A clinical photo of a skin lesion taken with a smartphone.
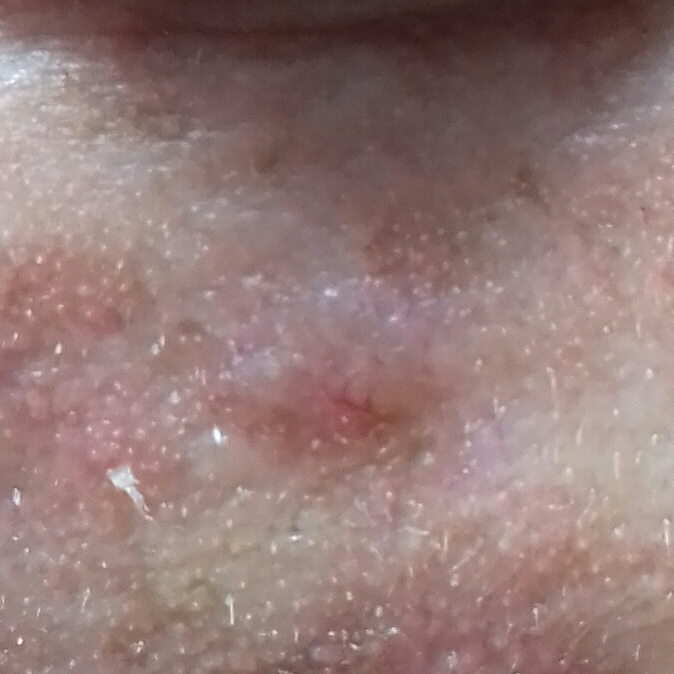The lesion involves the face.
The lesion measures 7 × 5 mm.
By the patient's account, the lesion is elevated and itches.
Histopathological examination showed a malignancy — a basal cell carcinoma.